The patient notes the lesion is raised or bumpy and fluid-filled; no relevant systemic symptoms; the patient notes the condition has been present for less than one week; male patient, age 30–39; the photo was captured at an angle.
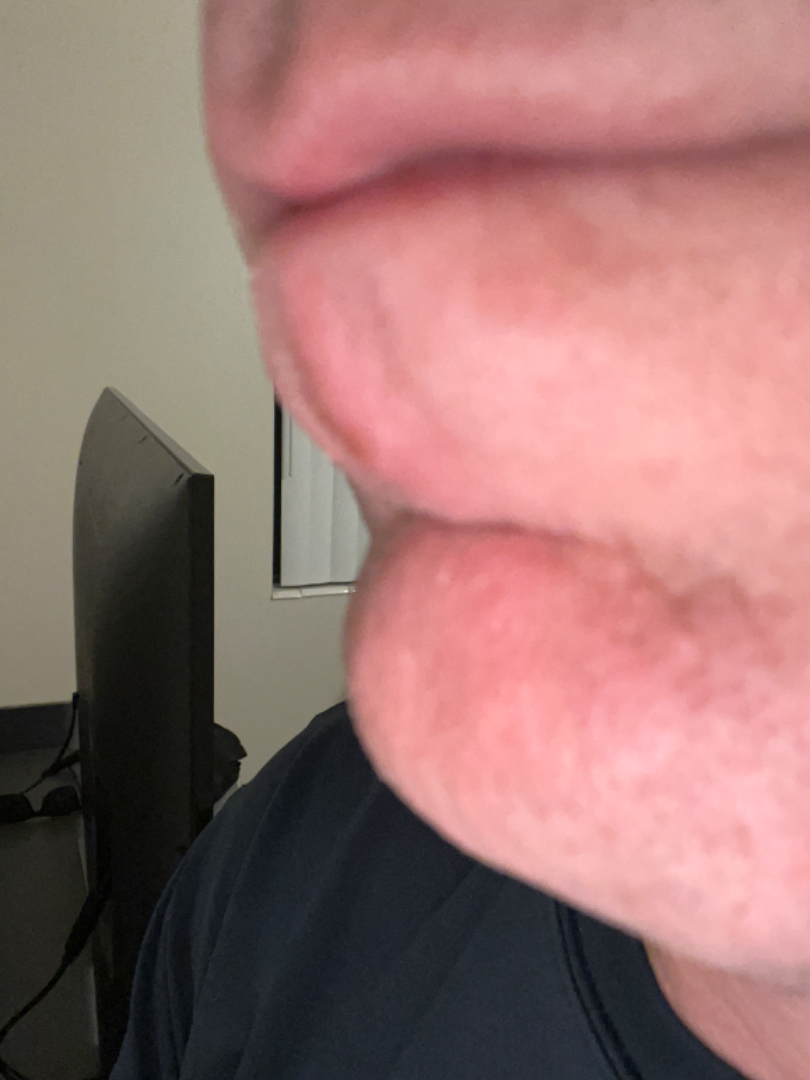{
  "differential": {
    "leading": [
      "Irritant Contact Dermatitis"
    ]
  }
}